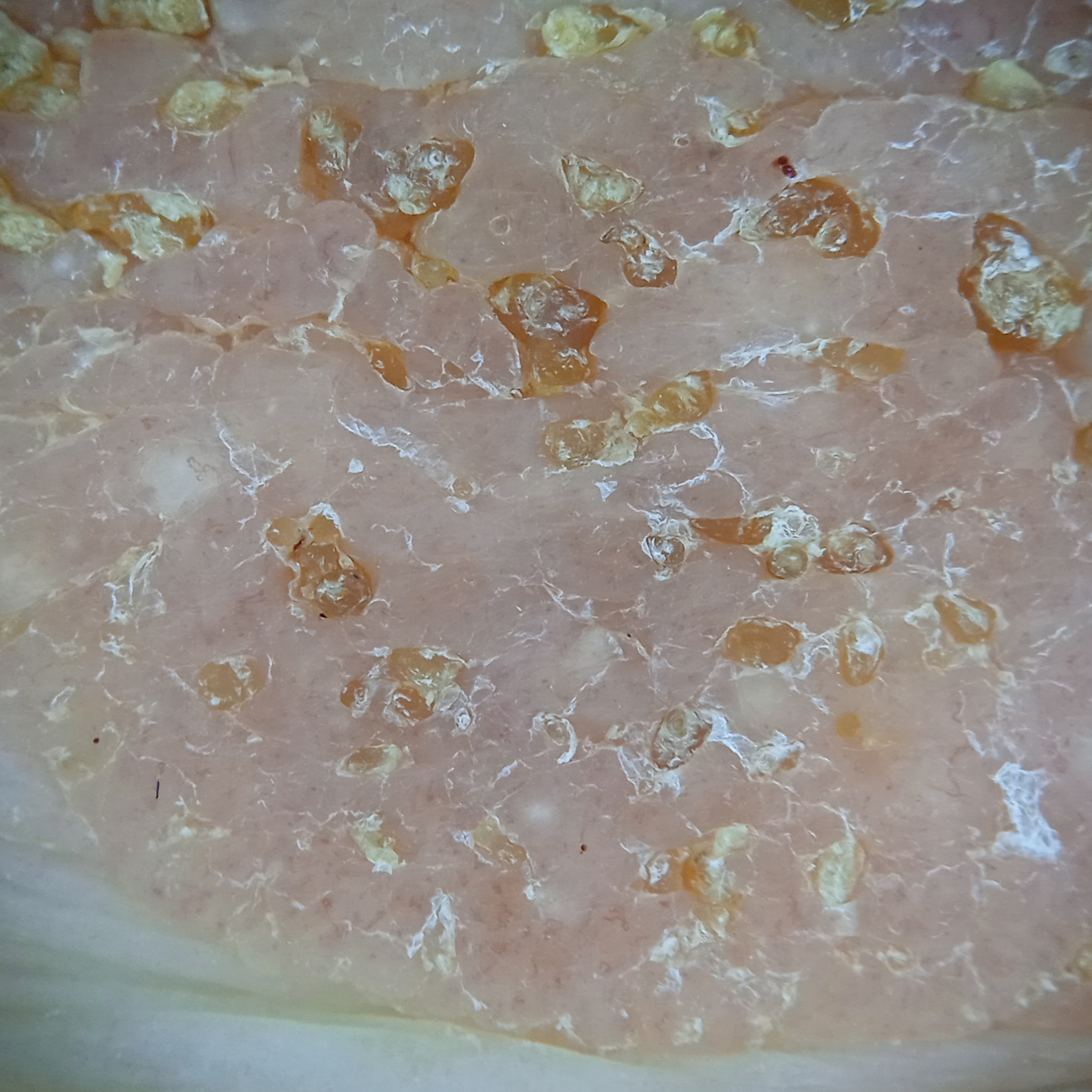Dermatologist review favored a seborrheic keratosis.